This is a dermoscopic photograph of a skin lesion. The subject is a male aged 58 to 62.
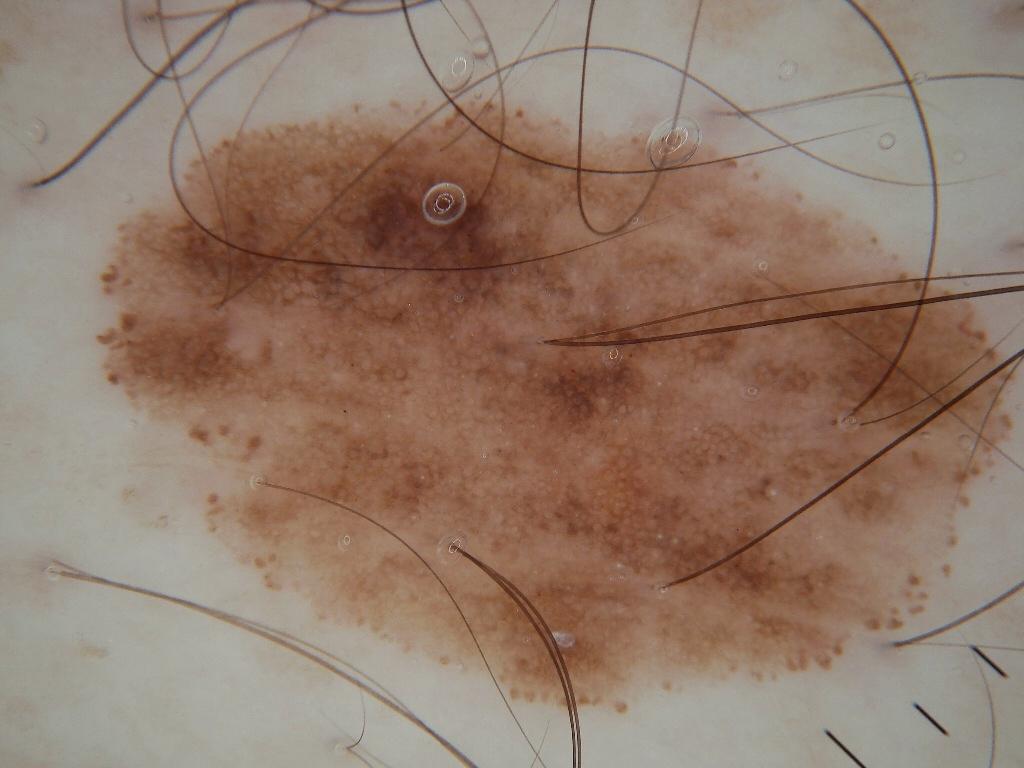Q: Which dermoscopic features were noted?
A: milia-like cysts, pigment network, and globules; absent: negative network and streaks
Q: Lesion extent?
A: ~55% of the field
Q: Where is the lesion located?
A: bbox=[90, 93, 1020, 718]
Q: What is this lesion?
A: a melanocytic nevus, a benign skin lesion